A dermoscopy image of a single skin lesion.
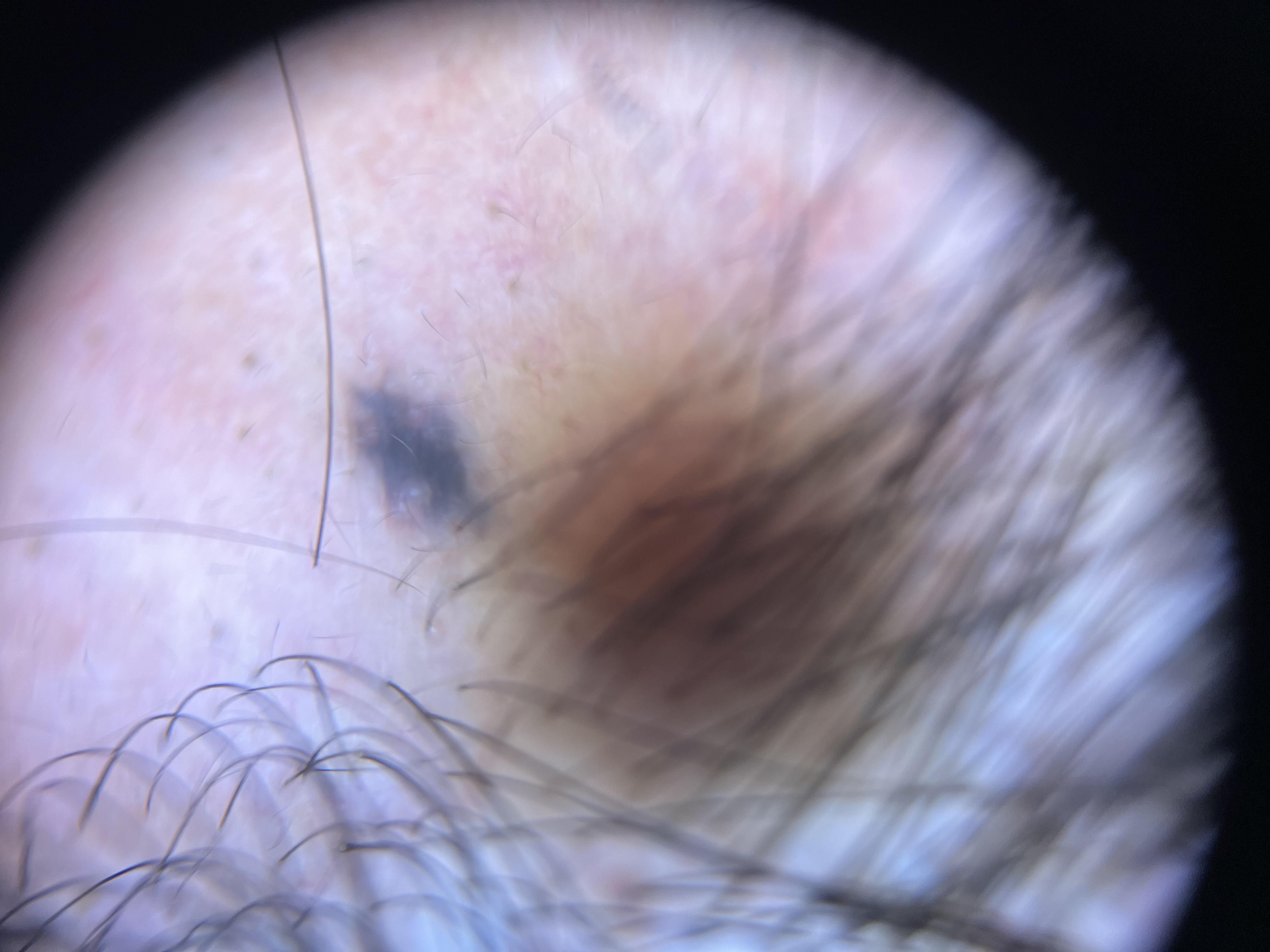The morphology is that of a banal, dermal lesion. Labeled as a blue nevus.